The subject is 18–29, female; the affected area is the leg; the photo was captured at a distance:
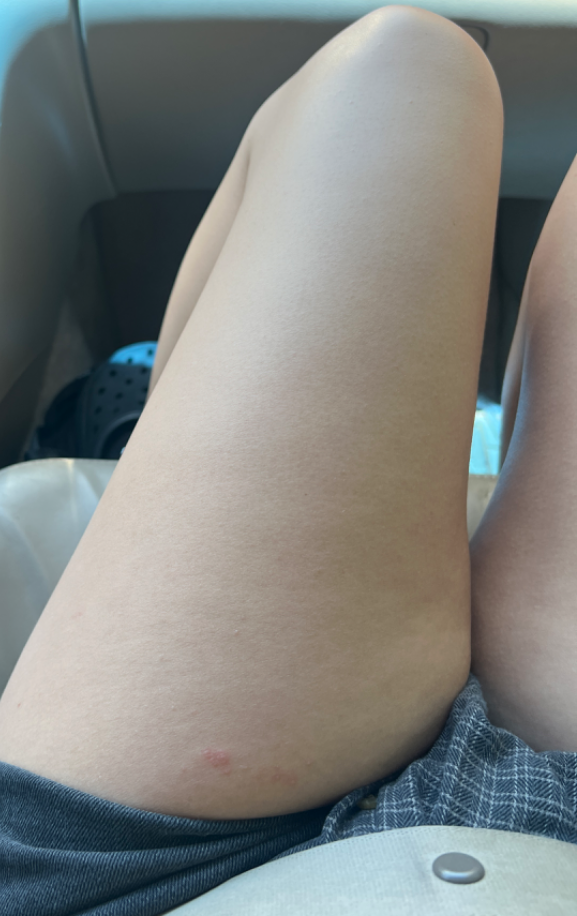patient's own categorization = a rash | symptom duration = about one day | symptoms = itching and bothersome appearance | texture = raised or bumpy | assessment = a single dermatologist reviewed the case: the differential, in no particular order, includes Folliculitis, Allergic Contact Dermatitis and Herpes Simplex.